This is a dermoscopic photograph of a skin lesion.
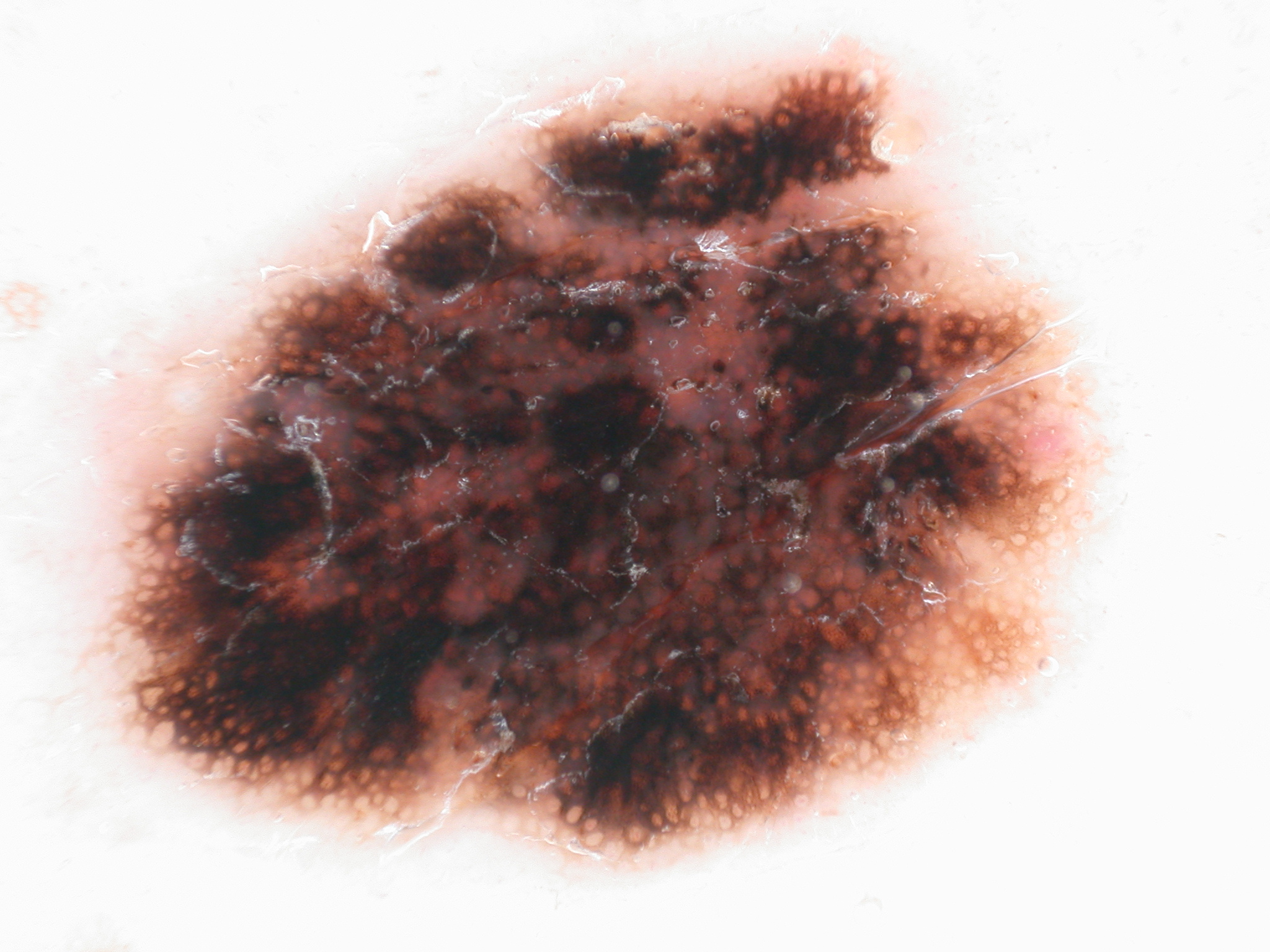Case summary: The dermoscopic pattern shows globules and pigment network; no streaks, milia-like cysts, or negative network. The lesion occupies roughly 51% of the field. With coordinates (x1, y1, x2, y2), the lesion occupies the region 83/37/1116/879. Conclusion: The diagnostic assessment was a melanocytic nevus, a benign lesion.